Close-up view. Female subject, age 30–39. Texture is reported as raised or bumpy. The contributor notes itching. The affected area is the top or side of the foot. Reported duration is less than one week. The patient described the issue as a rash: 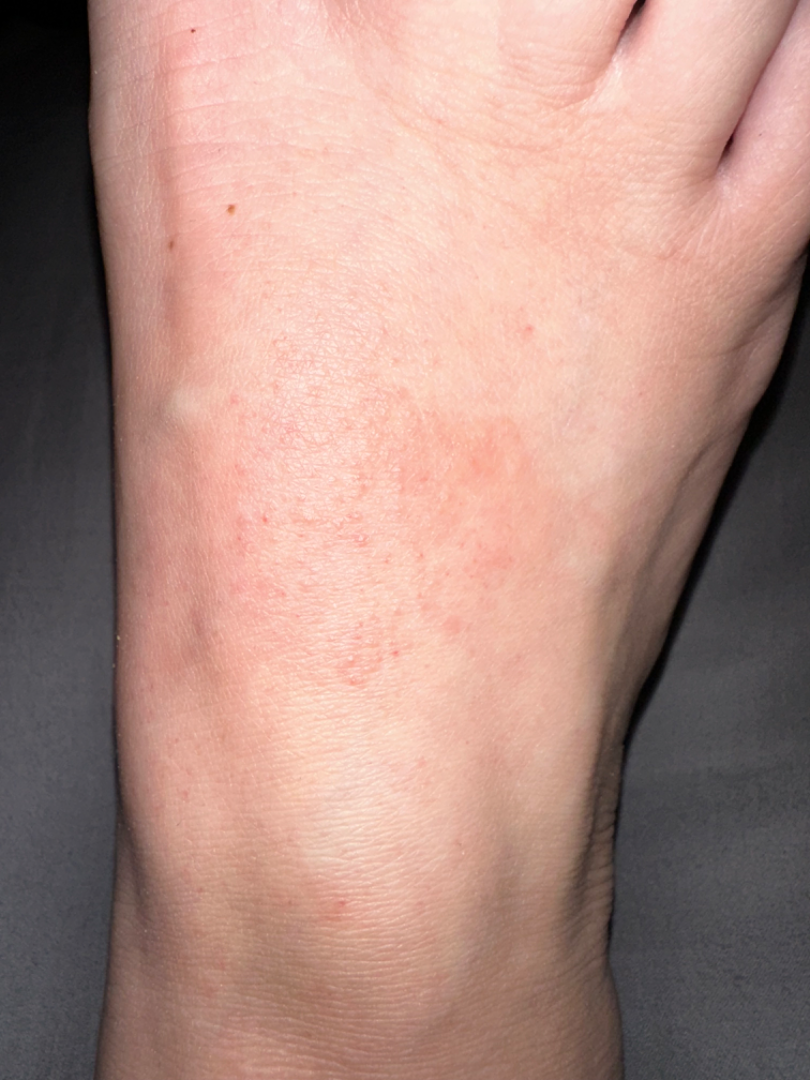| feature | finding |
|---|---|
| dermatologist impression | Contact dermatitis, Eczema, Lichen Simplex Chronicus and Allergic Contact Dermatitis were considered with similar weight; lower on the differential is Pigmented purpuric eruption |